A dermoscopic image of a skin lesion, the patient is a female aged 63-67:
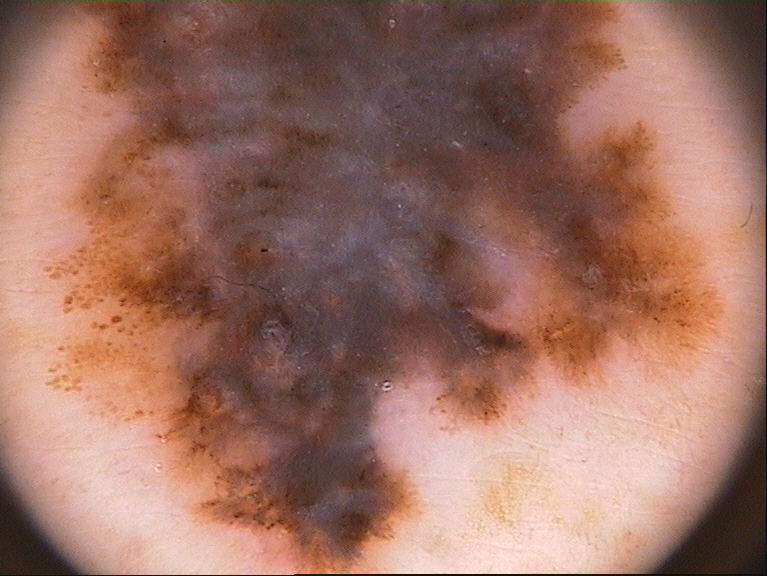lesion size: large
dermoscopic features: globules
lesion bbox: [38, 1, 728, 571]
diagnostic label: a melanoma